Recorded as Fitzpatrick skin type III · a female subject approximately 55 years of age: 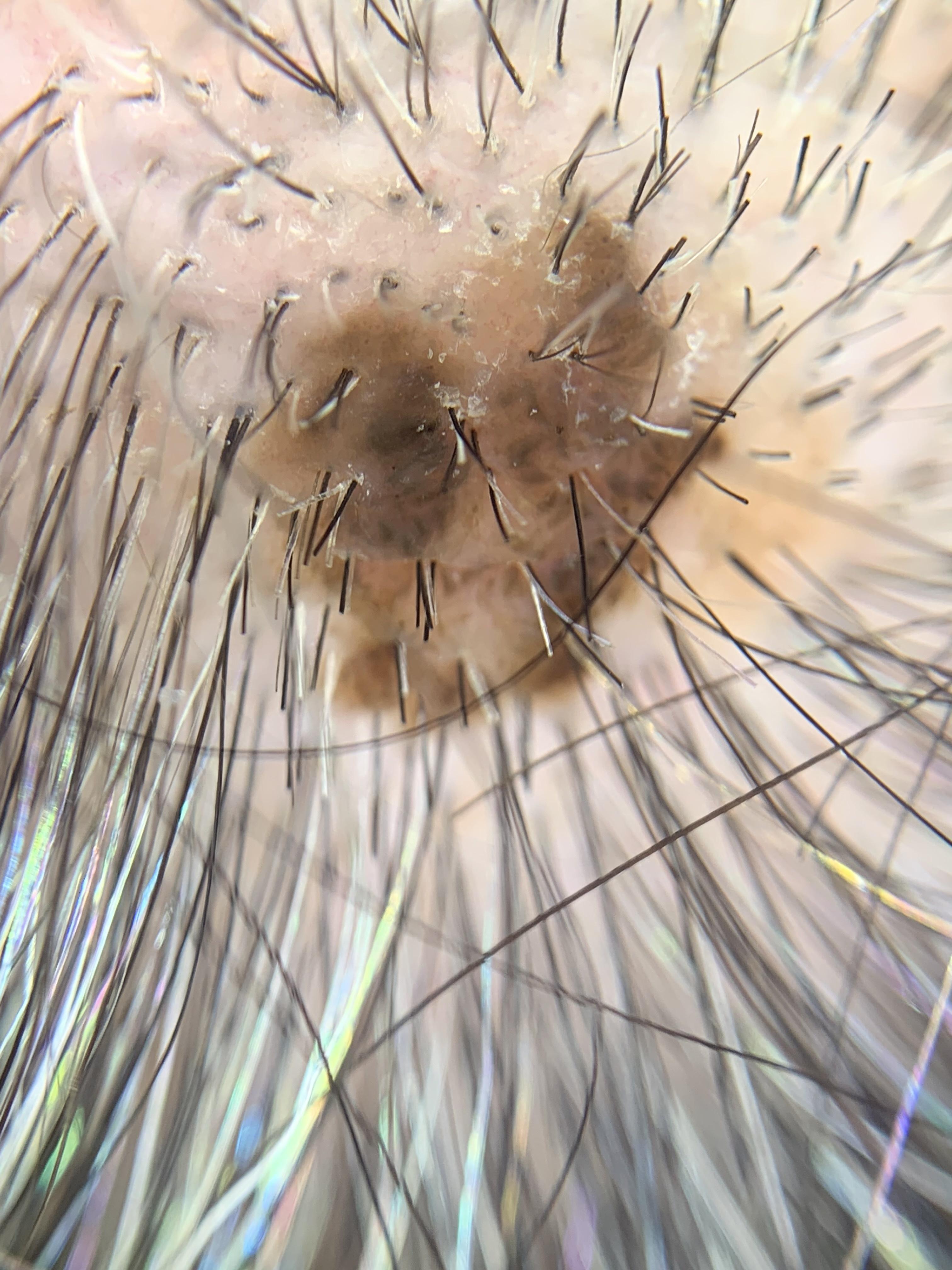Pathology: The biopsy diagnosis was an epidermal lesion — a seborrheic keratosis.